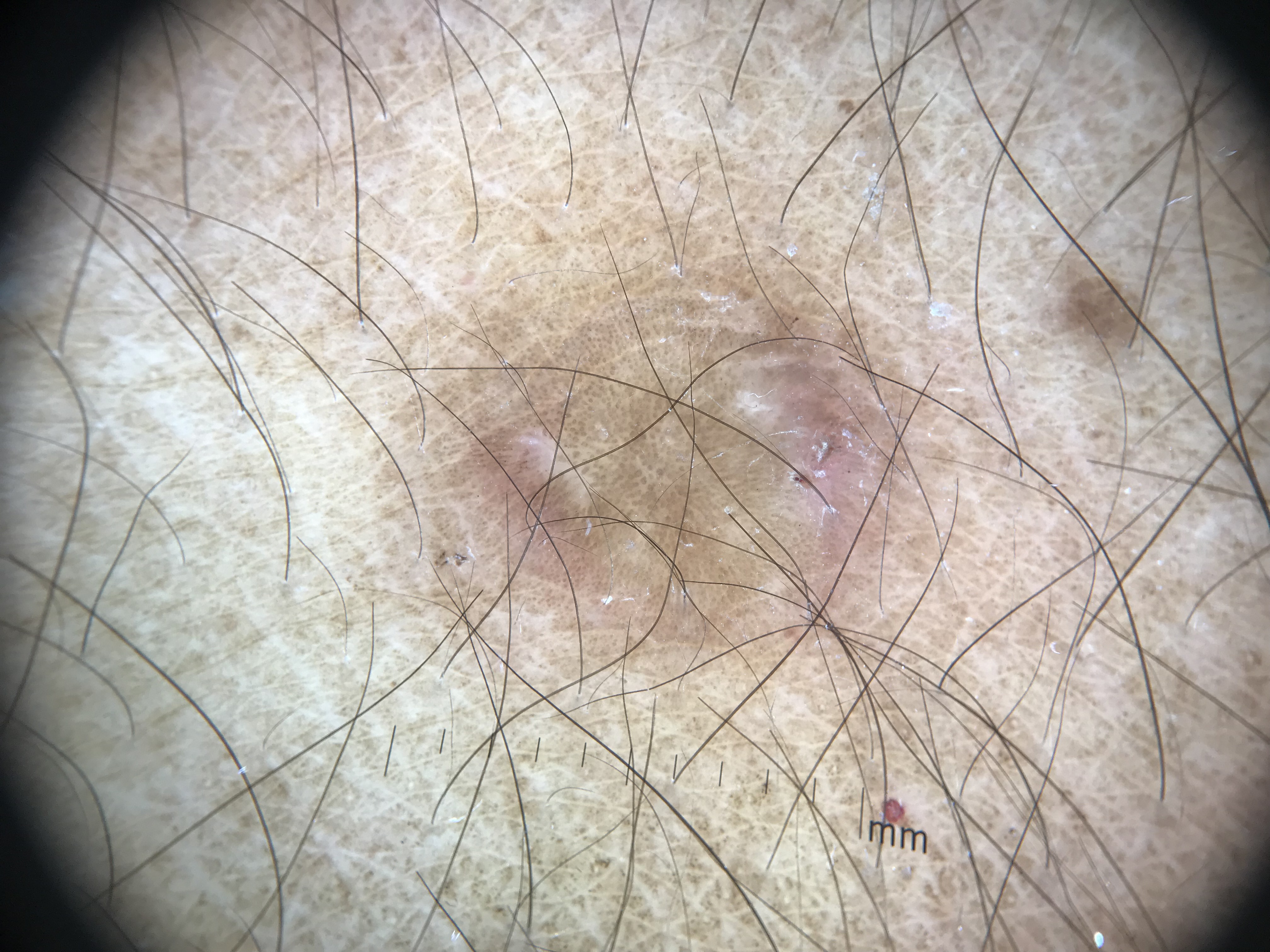Q: What is this lesion?
A: dermatofibroma (expert consensus)